Located on the arm and leg. The lesion is associated with burning and itching. The patient described the issue as a rash. An image taken at a distance. The patient indicates the lesion is flat. The condition has been present for one to four weeks. The patient also reports fatigue:
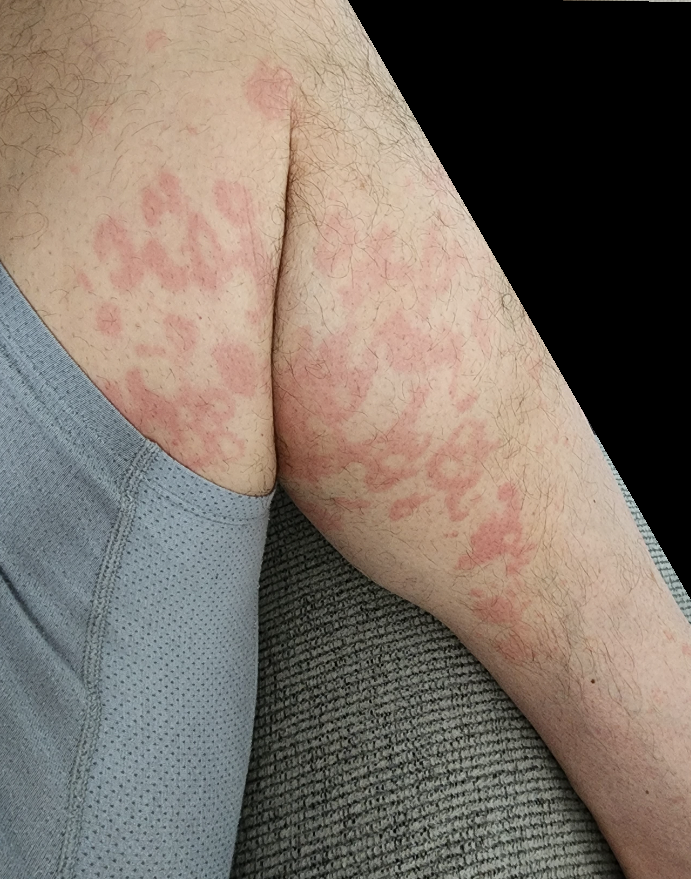The reviewing clinician's impression was: Urticaria (most likely); Granuloma annulare (possible); Cutaneous lupus (possible).